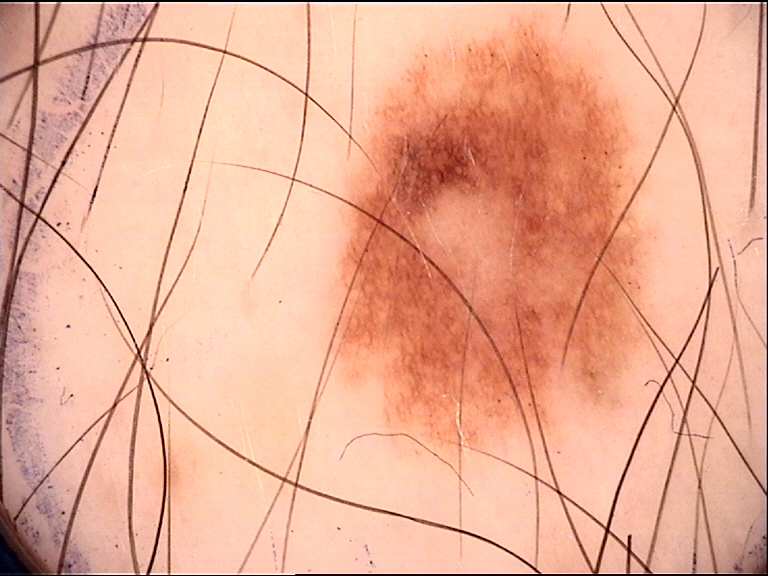Labeled as a dysplastic junctional nevus.